A female patient aged 81 · acquired for a research image collection, with no referral diagnosis · the patient describes having a moderate number of moles · the patient says their skin reddens painfully with sun exposure · a clinical close-up of a skin lesion: 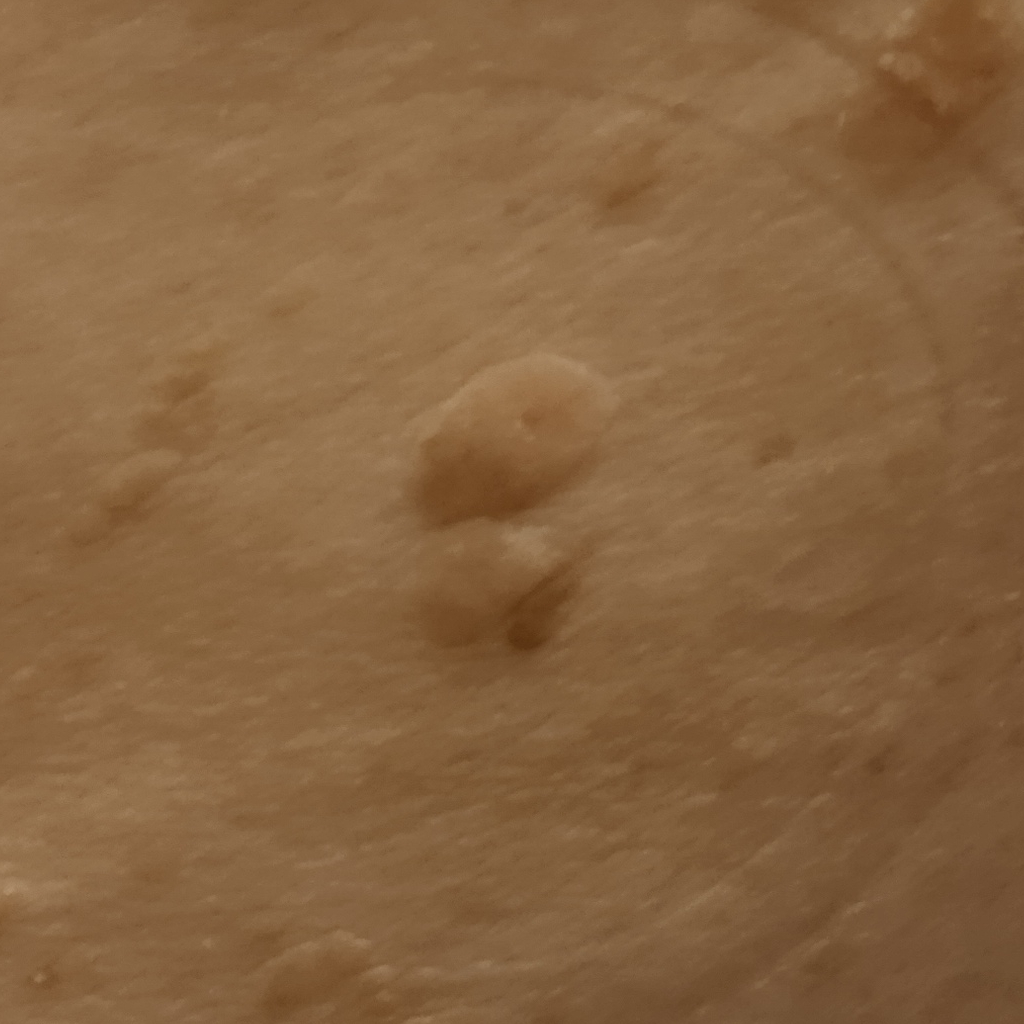{"lesion_location": "the back", "lesion_size": {"diameter_mm": 15.5}, "diagnosis": {"name": "seborrheic keratosis", "malignancy": "benign"}}